This is a close-up image; located on the front of the torso and arm; the lesion is associated with itching; the condition has been present for less than one week; the patient considered this a rash:
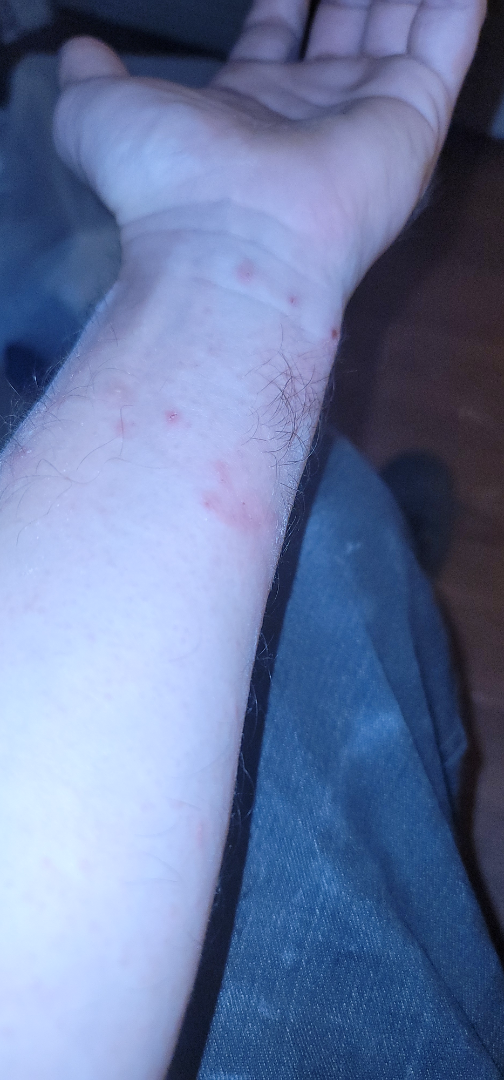  differential:
    leading:
      - Eczema
    considered:
      - Tinea
      - Psoriasis